The subject is a female aged approximately 25; dermoscopy of a skin lesion — 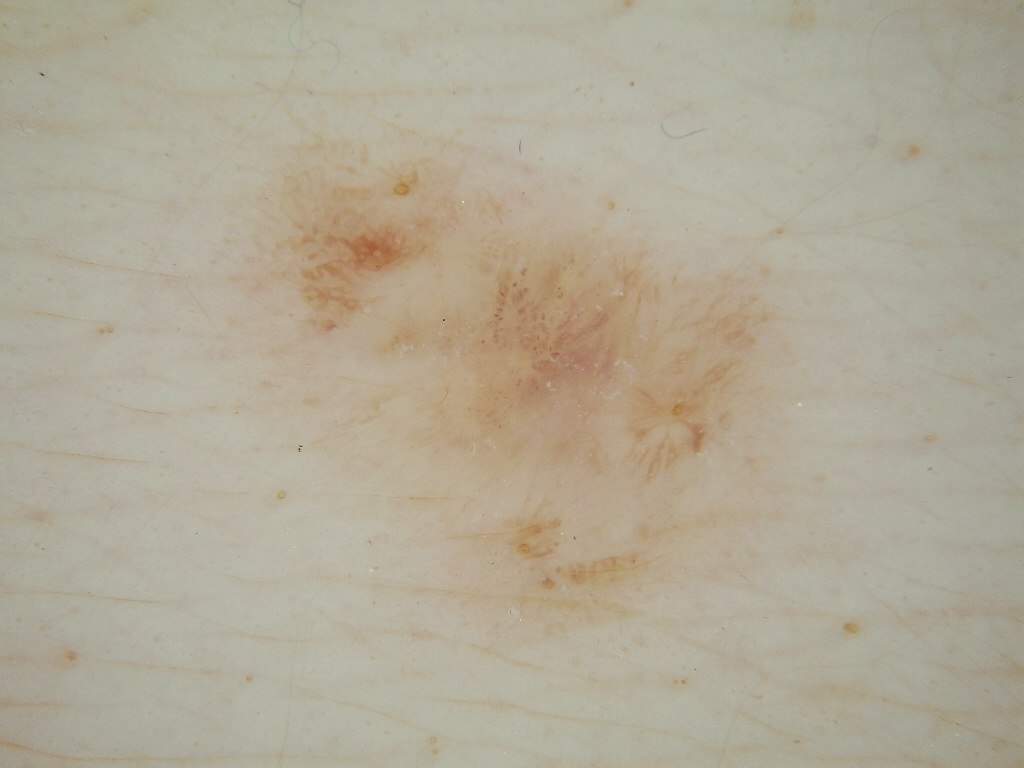Dermoscopic examination shows pigment network and globules; no milia-like cysts, negative network, or streaks. The lesion is bounded by bbox(196, 95, 794, 645). Consistent with a melanocytic nevus, a benign lesion.